No associated systemic symptoms reported. Located on the arm. Reported lesion symptoms include itching. The photograph is a close-up of the affected area. Self-categorized by the patient as a rash. The lesion is described as raised or bumpy. The condition has been present for about one day.
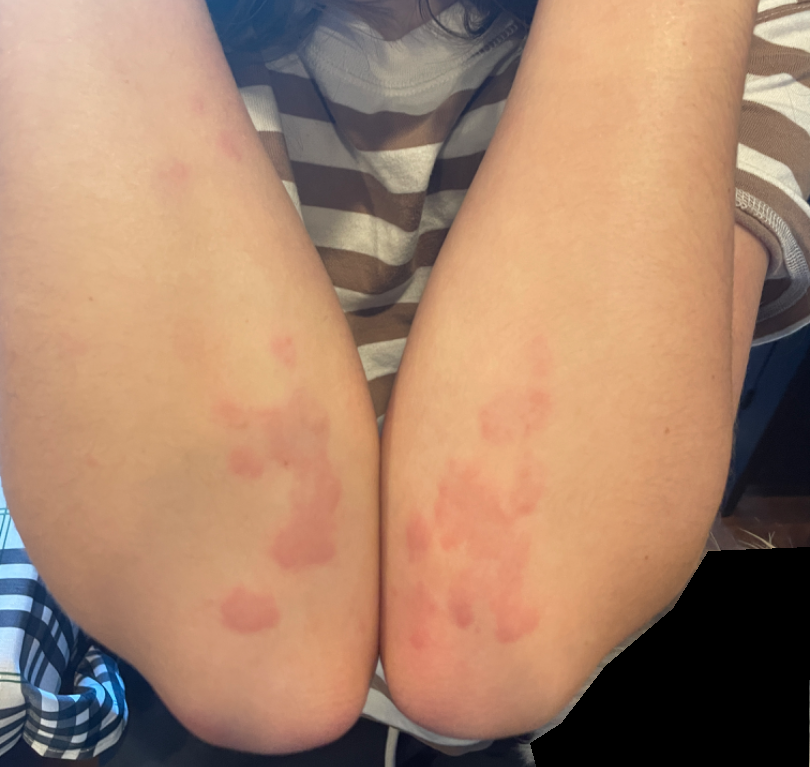diagnostic considerations = the leading impression is Urticaria; possibly Eczema.